A dermoscopic image of a skin lesion.
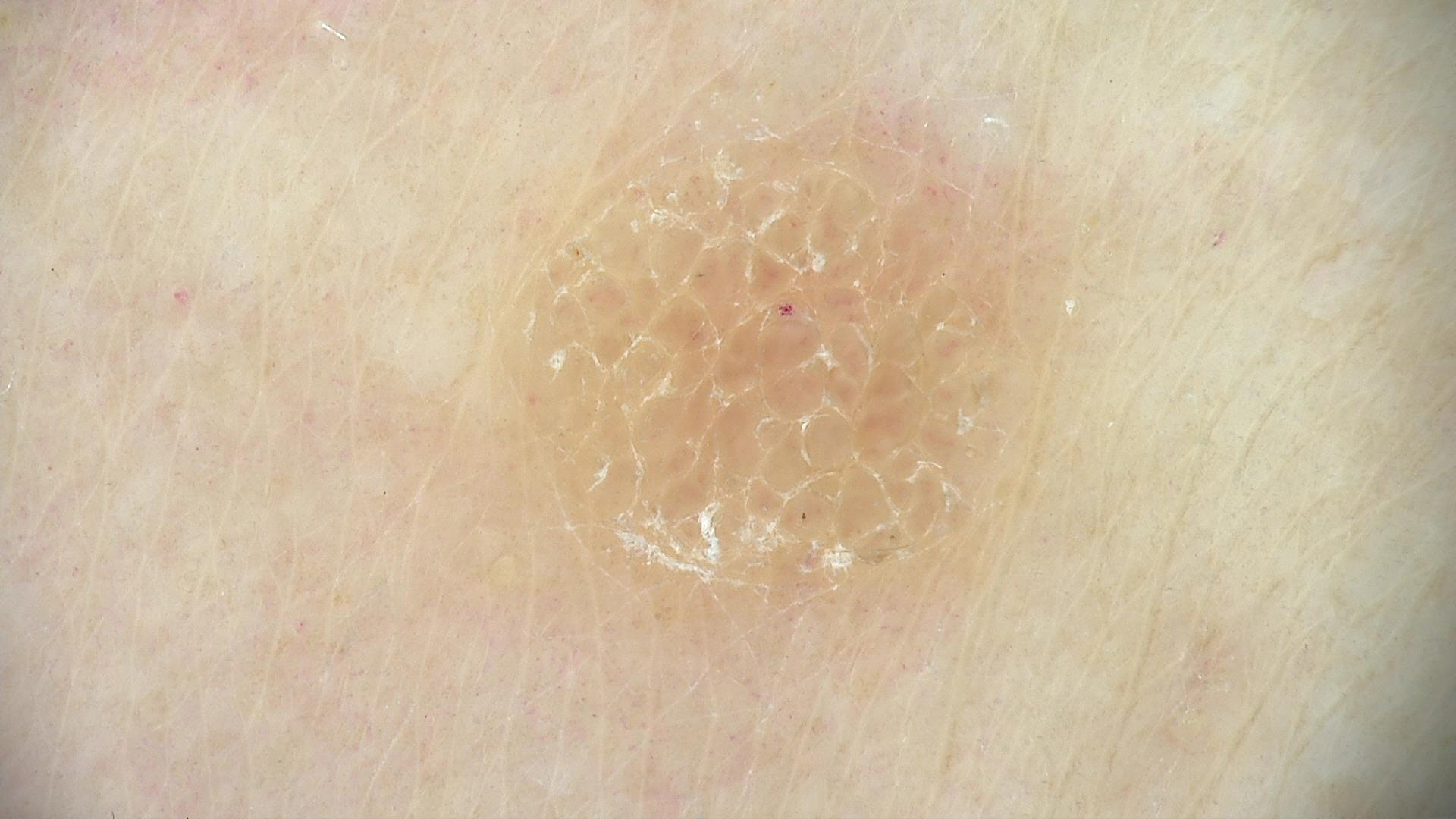Labeled as a keratinocytic lesion — a seborrheic keratosis.